A dermatoscopic image of a skin lesion.
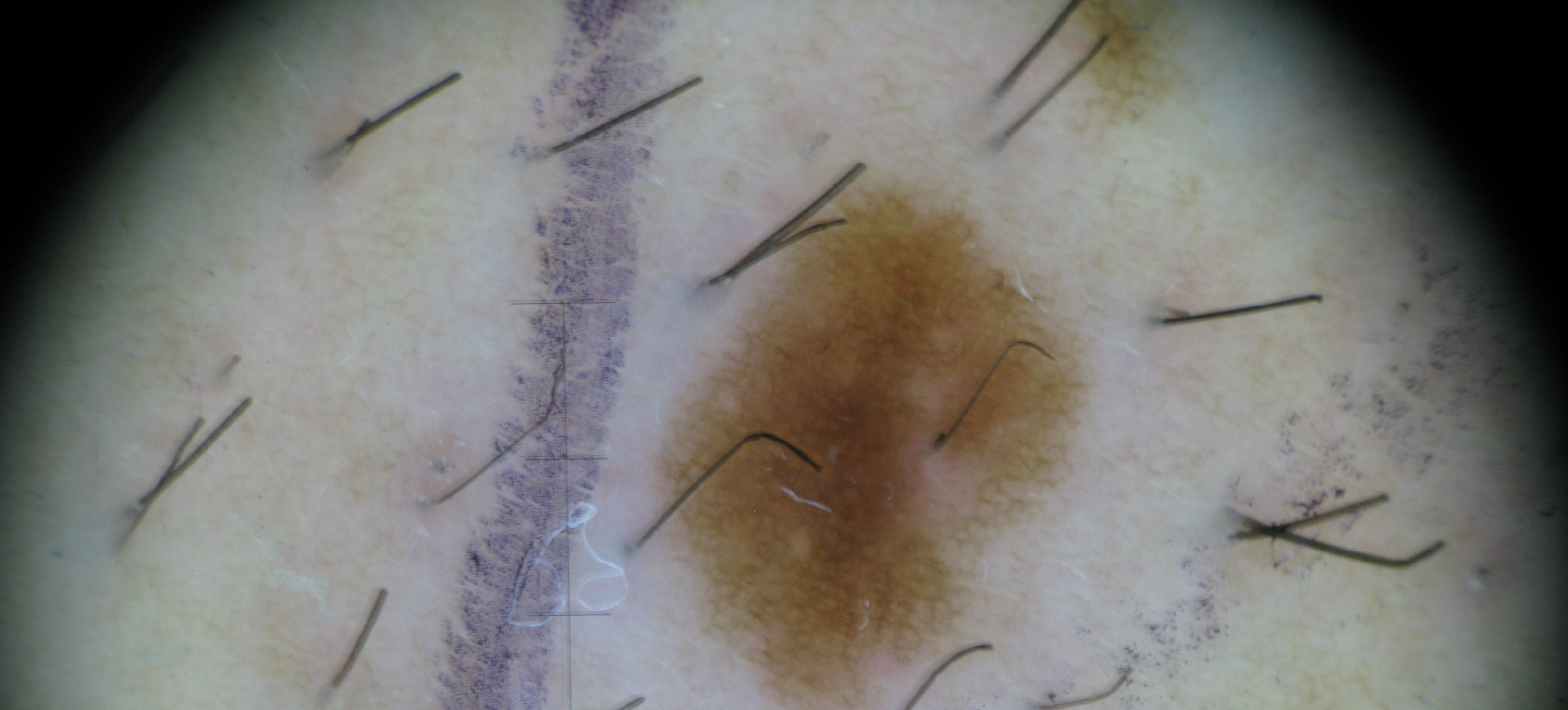The architecture is that of a banal lesion. The diagnosis was a junctional nevus.